A dermoscopic close-up of a skin lesion, the patient is a female aged 58-62.
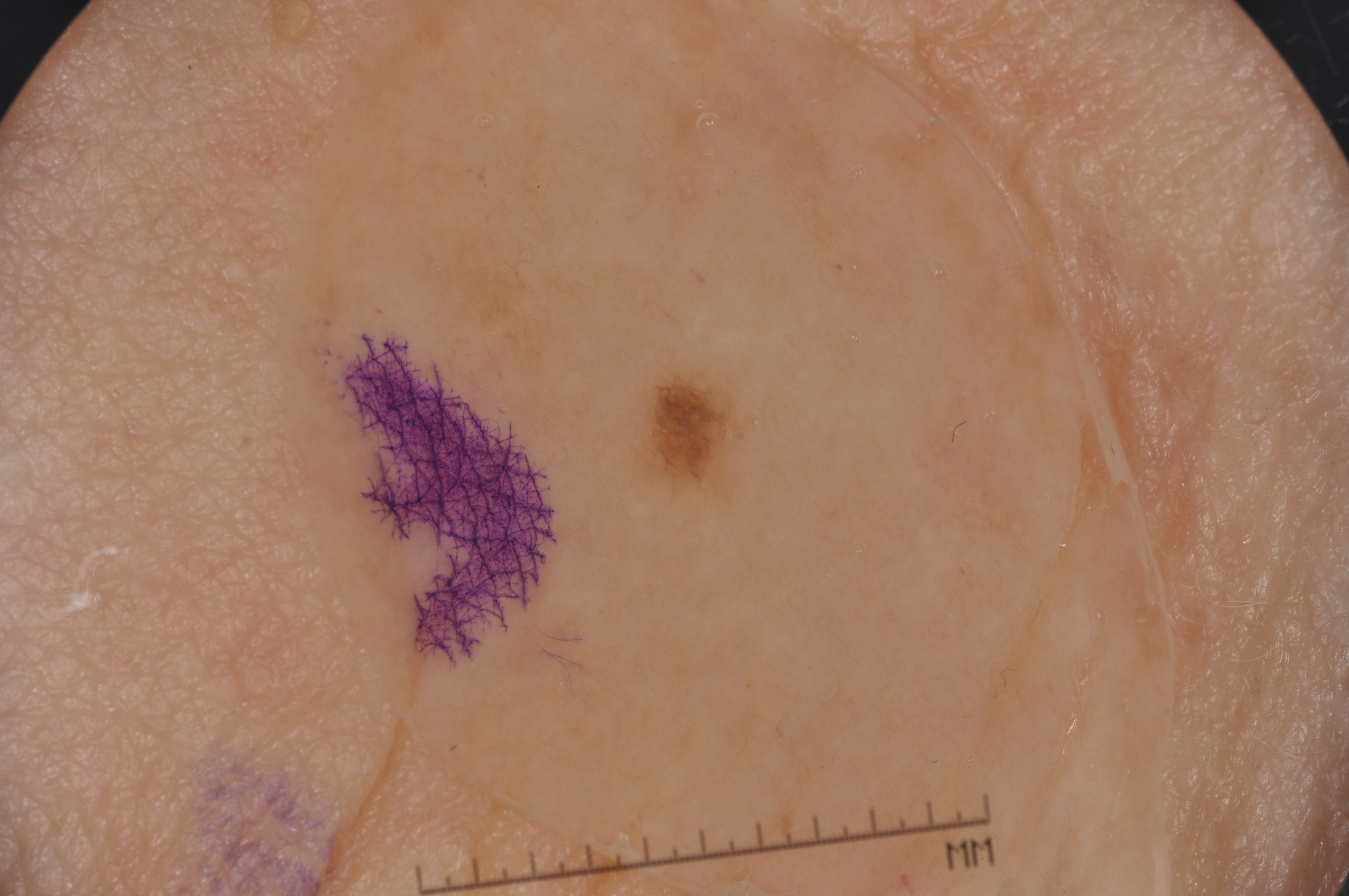In (x1, y1, x2, y2) order, lesion location: 630/367/745/505. The dermoscopic pattern shows pigment network. Consistent with a melanocytic nevus, a benign skin lesion.